The patient is FST III:
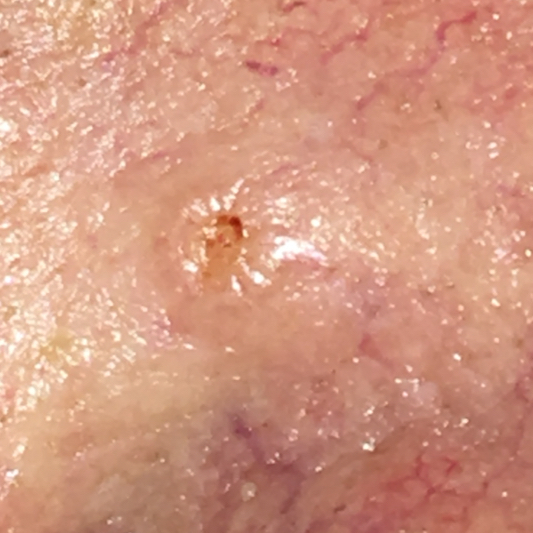Findings:
• reported symptoms · growth, elevation, bleeding, change in appearance
• pathology · basal cell carcinoma (biopsy-proven)